The chart records prior malignancy (patient or family) and tobacco use. A clinical photo of a skin lesion taken with a smartphone. Fitzpatrick II:
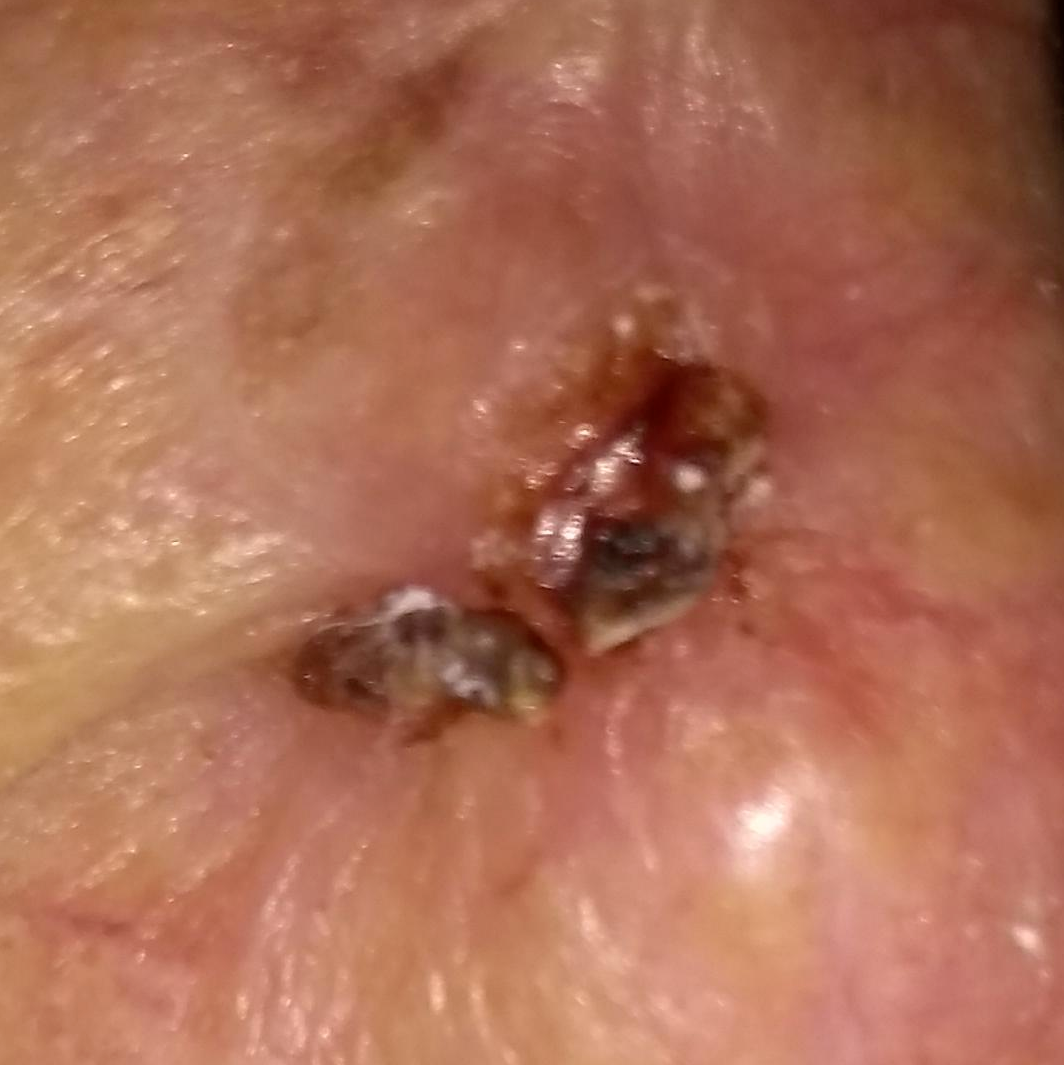Clinical context:
The lesion is located on the nose. Measuring about 13 × 3 mm. Per patient report, the lesion itches, is elevated, has bled, hurts, and has grown.
Diagnosis:
Histopathological examination showed a basal cell carcinoma.